The contributor is a female aged 30–39. The photograph was taken at an angle. Located on the arm:
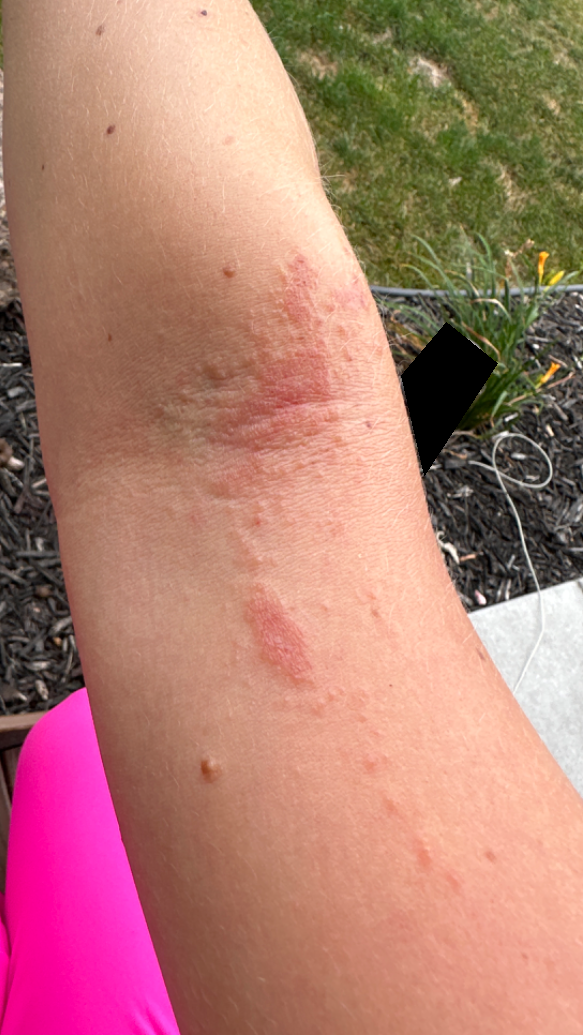history: one to four weeks | lesion texture: raised or bumpy, rough or flaky and fluid-filled | patient describes the issue as: a rash | clinical impression: most likely Eczema; also raised was Allergic Contact Dermatitis.